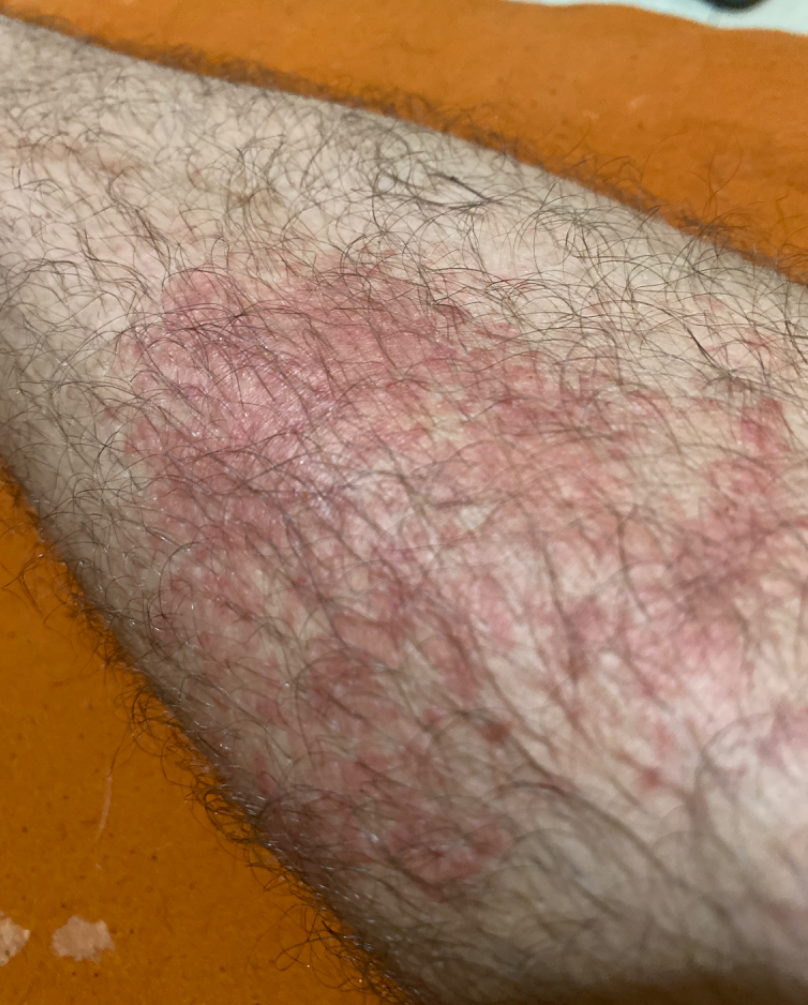assessment: indeterminate from the photograph | affected area: leg | shot type: close-up.